This image was taken at an angle; the affected area is the front of the torso:
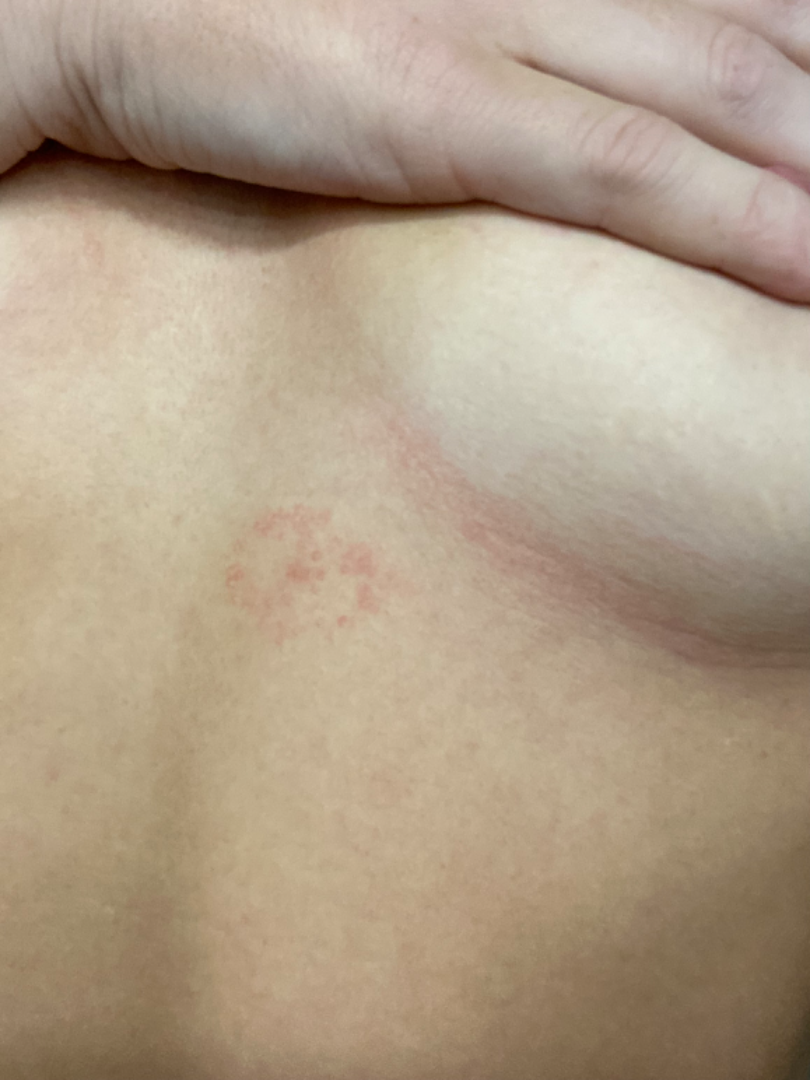patient describes the issue as: a rash | onset: about one day | lesion texture: raised or bumpy | patient-reported symptoms: bothersome appearance | differential diagnosis: the primary impression is Tinea; possibly Eczema; also raised was Irritant Contact Dermatitis.